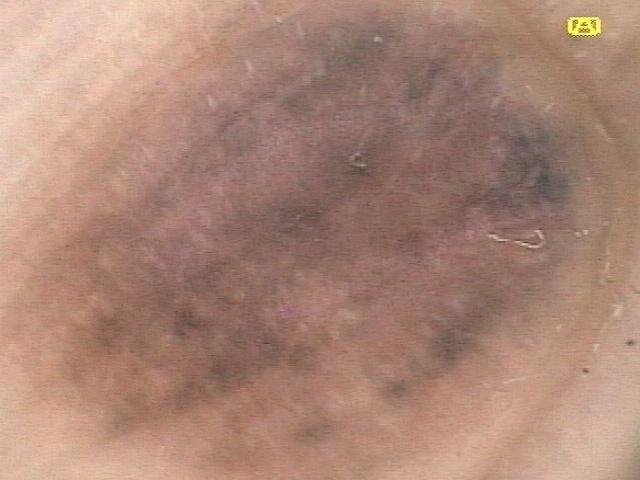Fitzpatrick II.
Dermoscopy of a skin lesion.
The lesion is located on an acral site (palms or soles).
Clinically diagnosed as a lesion of melanocytic origin — a nevus.